A skin lesion imaged with a dermatoscope.
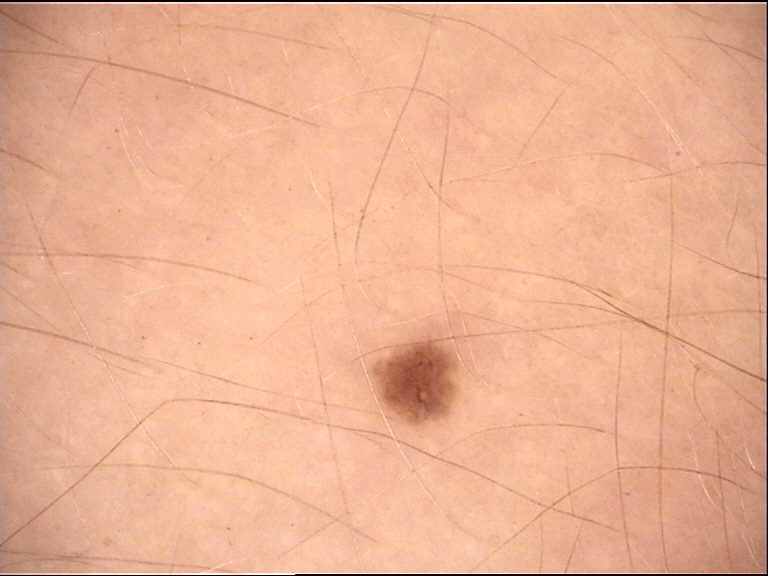Findings:
This is a banal lesion.
Impression:
The diagnosis was a junctional nevus.